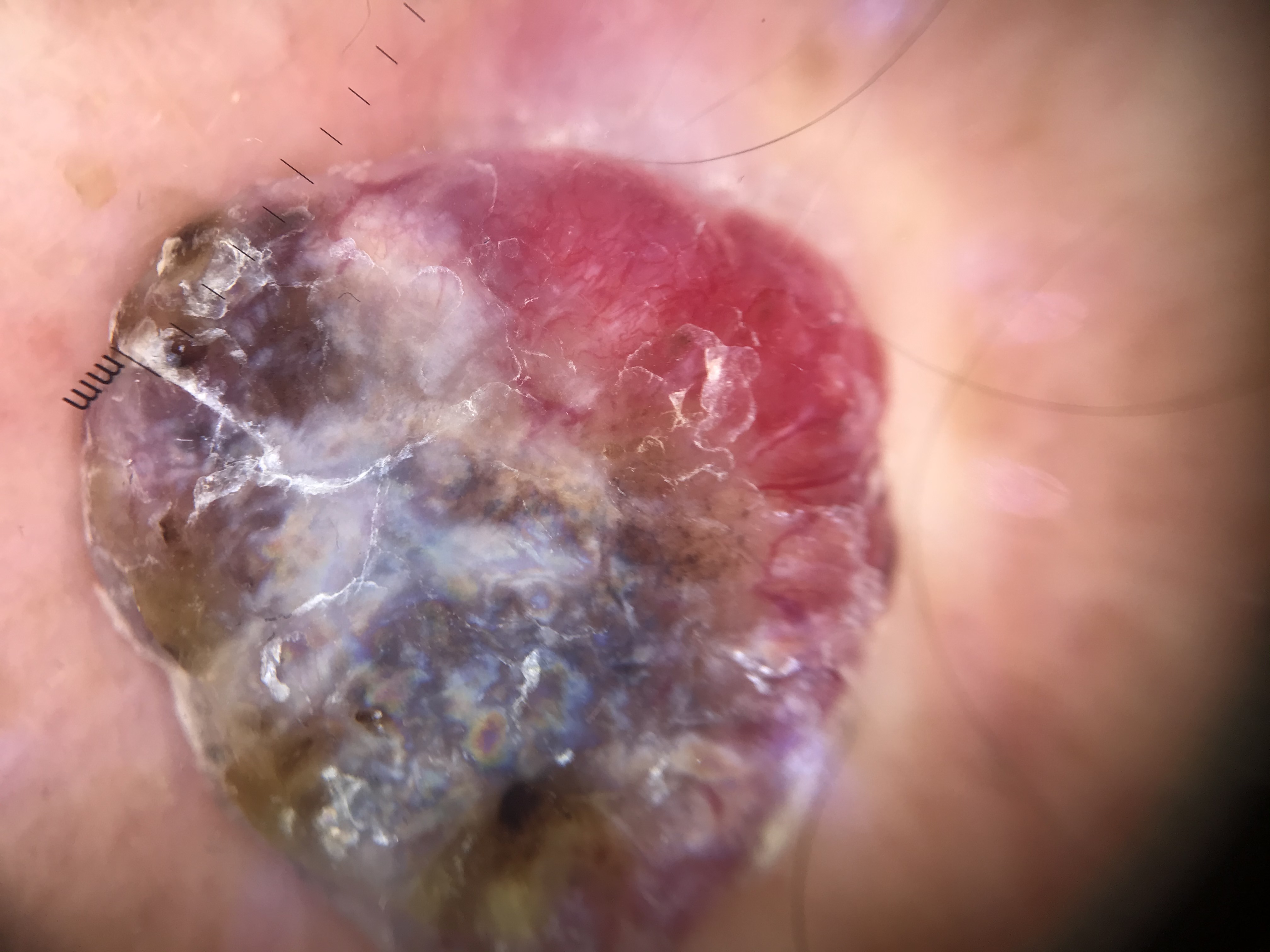image type — dermatoscopy; diagnostic label — melanoma (biopsy-proven).